The patient was assessed as Fitzpatrick phototype I. The chart notes a prior melanoma. A dermatoscopic image of a skin lesion — 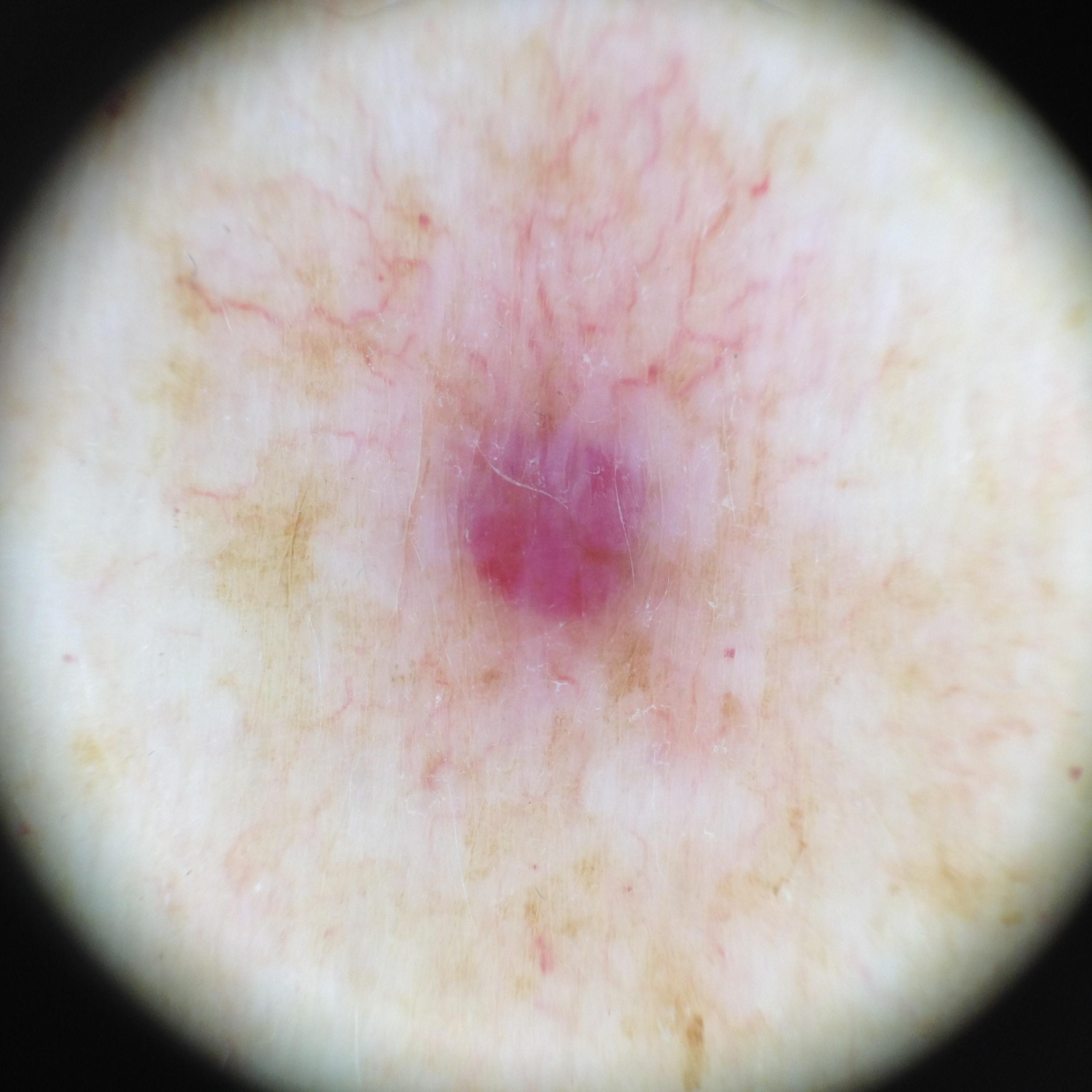The lesion involves the trunk, specifically the anterior trunk.
Clinically diagnosed as a benign vascular lesion.